A skin lesion imaged with a dermatoscope.
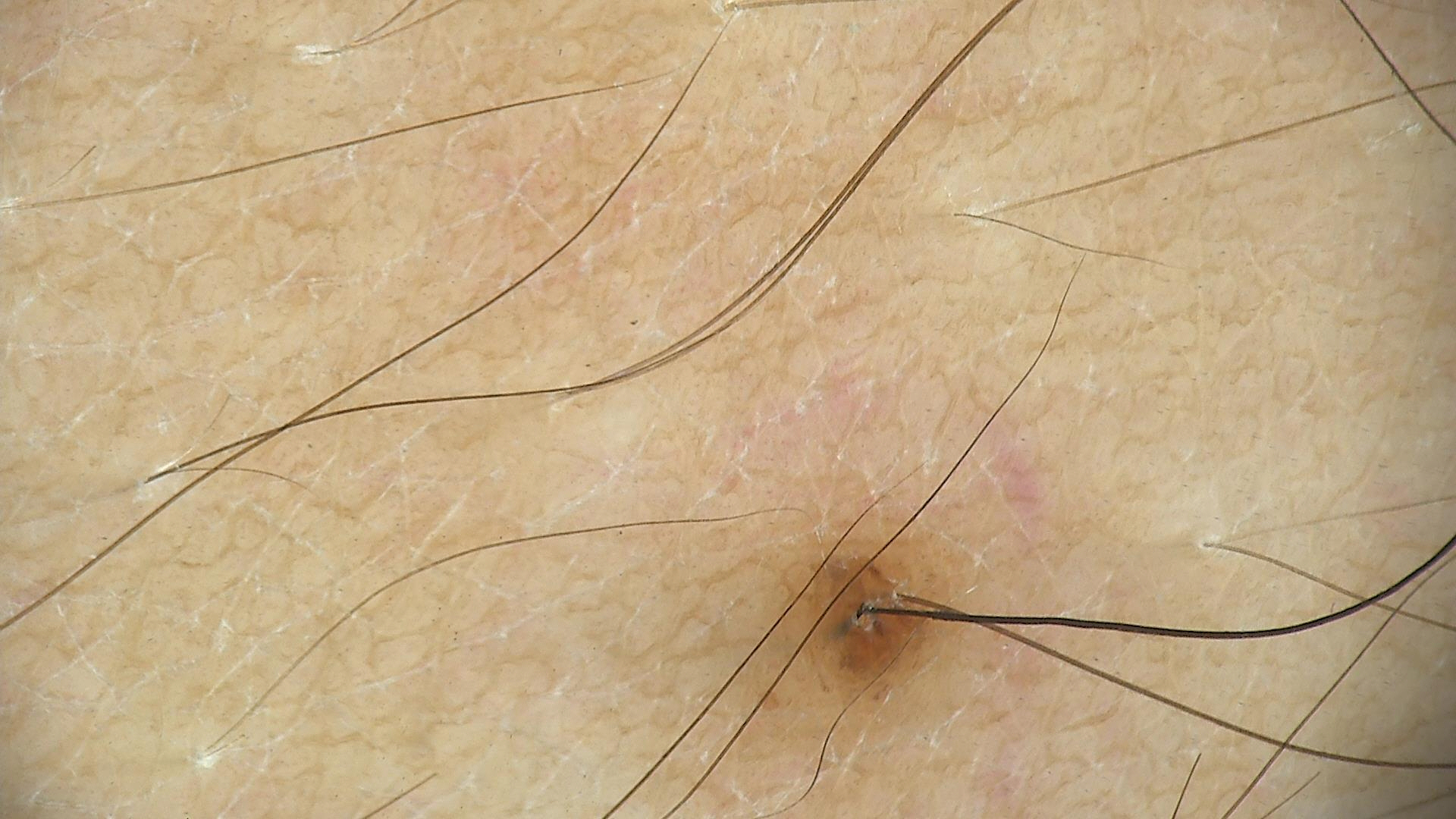lesion type=banal | assessment=junctional nevus (expert consensus).